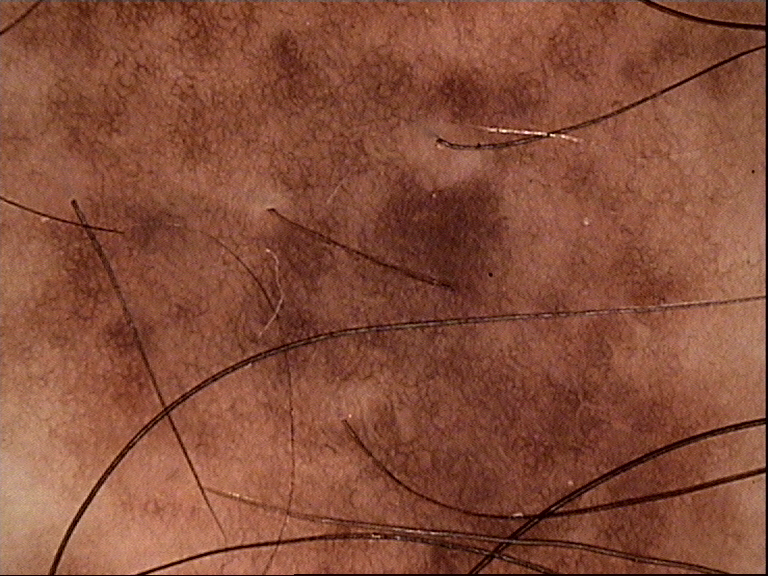Summary: A dermoscopy image of a single skin lesion. This is a banal lesion. Conclusion: Classified as a congenital compound nevus.